A contact-polarized dermoscopy image of a skin lesion; a female subject aged approximately 55 — 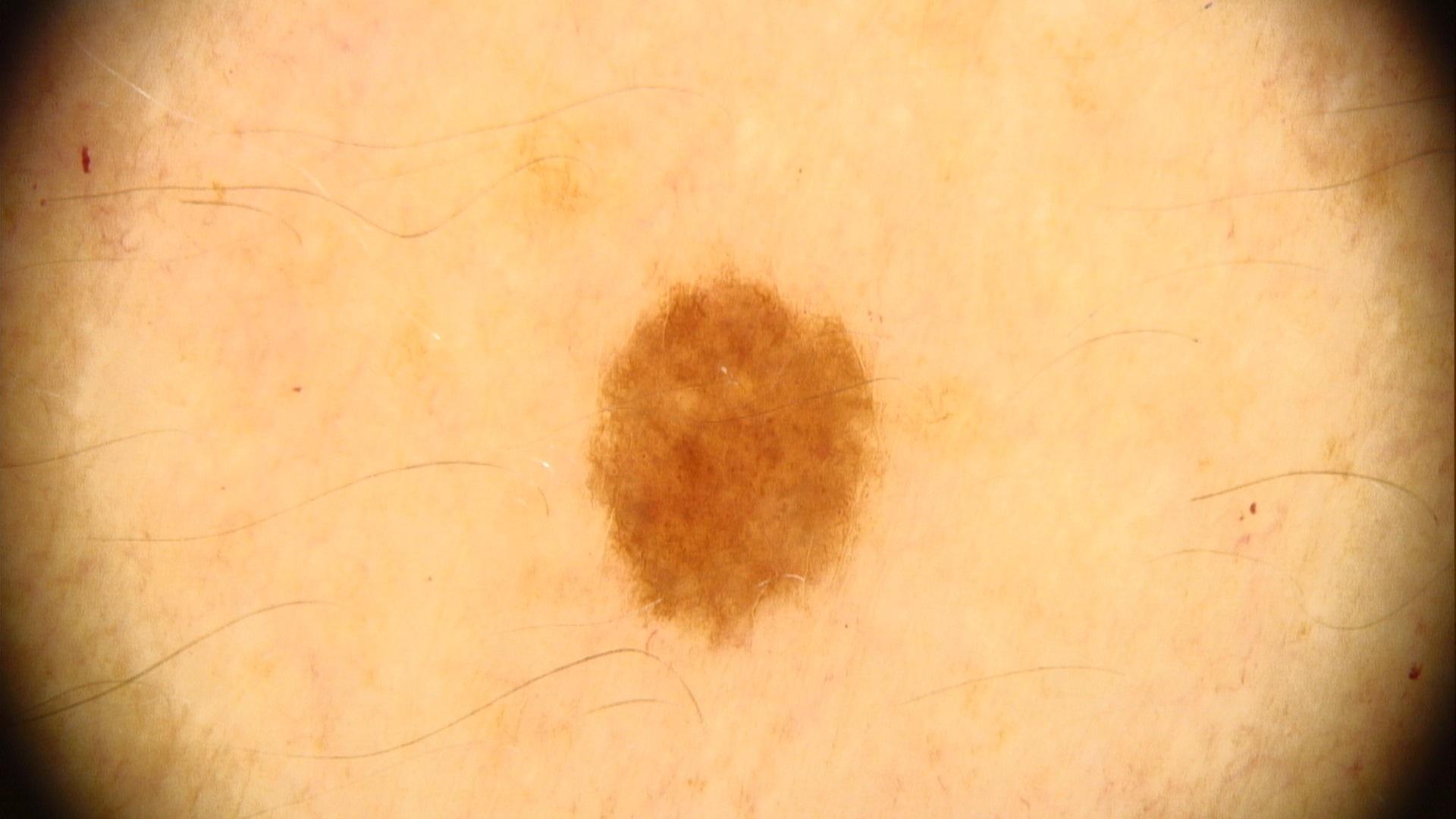Image and clinical context:
The lesion is on an upper extremity.
Conclusion:
Expert review favored a nevus.